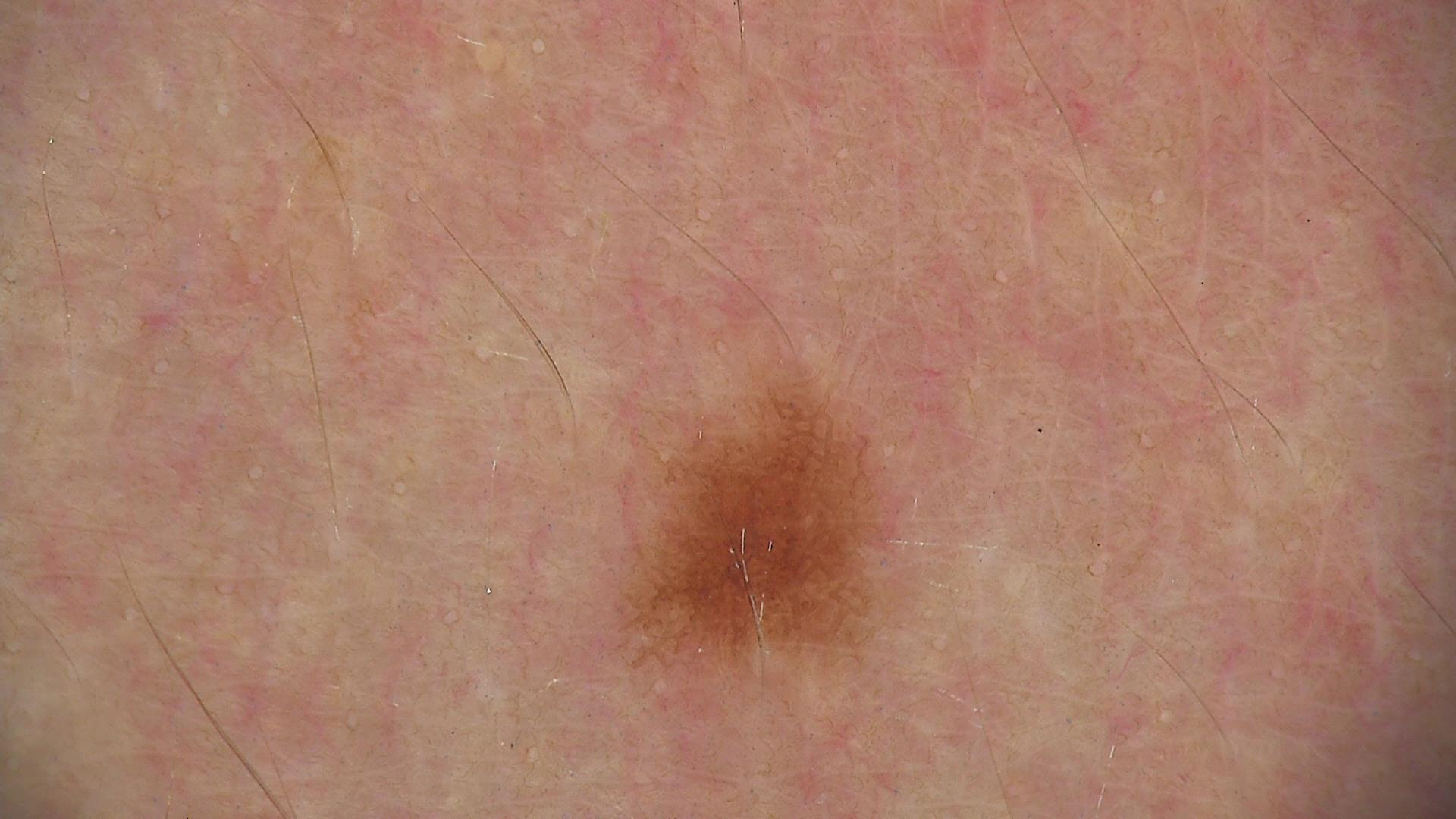A dermoscopy image of a single skin lesion. Consistent with a banal lesion — a junctional nevus.